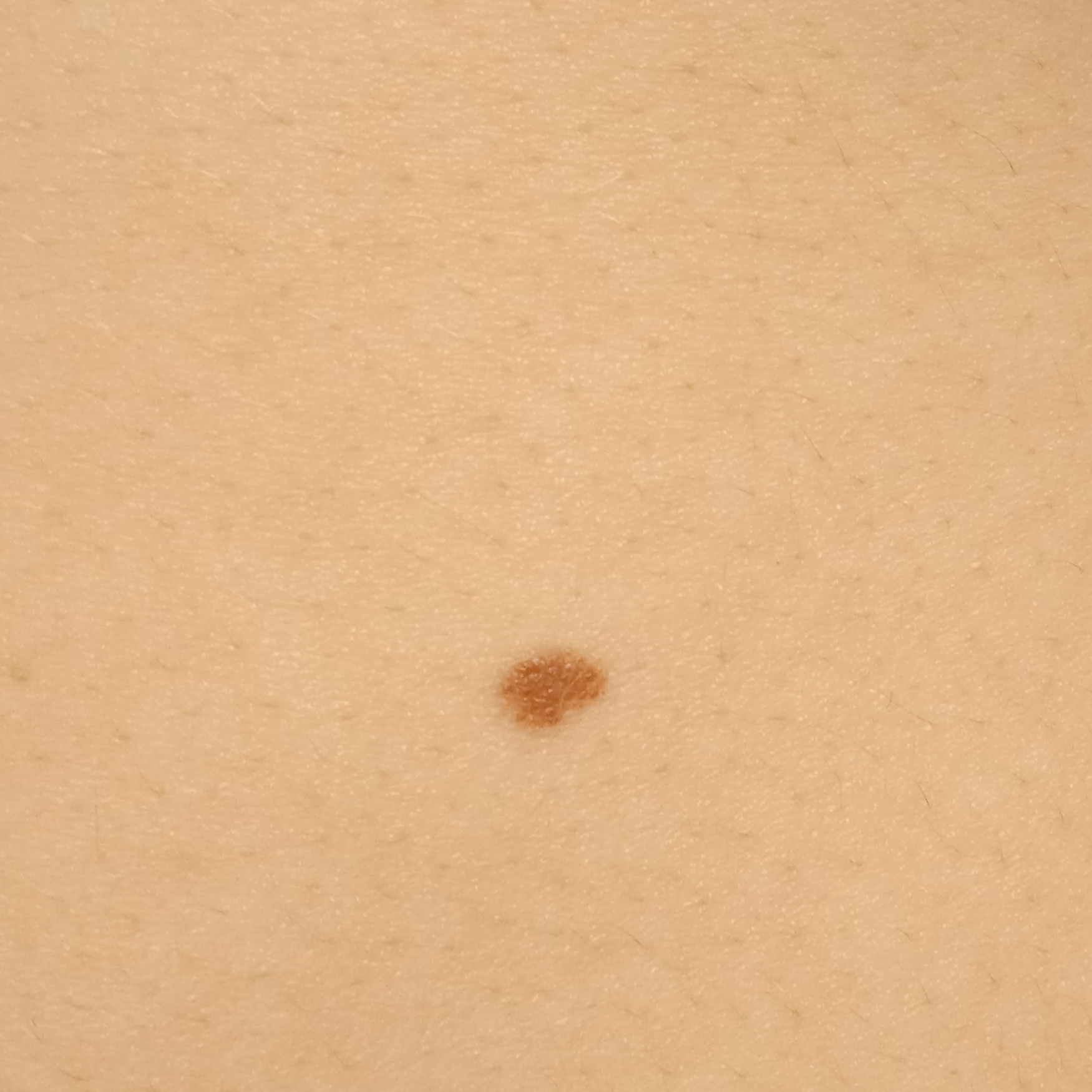Summary:
A moderate number of moles by the patient's own estimate. A female patient age 20. A clinical photograph showing a skin lesion. Acquired for a research image collection, with no referral diagnosis. The patient says their skin reddens with sun exposure. On a questionnaire the patient reported no sunbed use. The lesion involves the torso.
Conclusion:
The consensus diagnosis for this lesion was a melanocytic nevus.